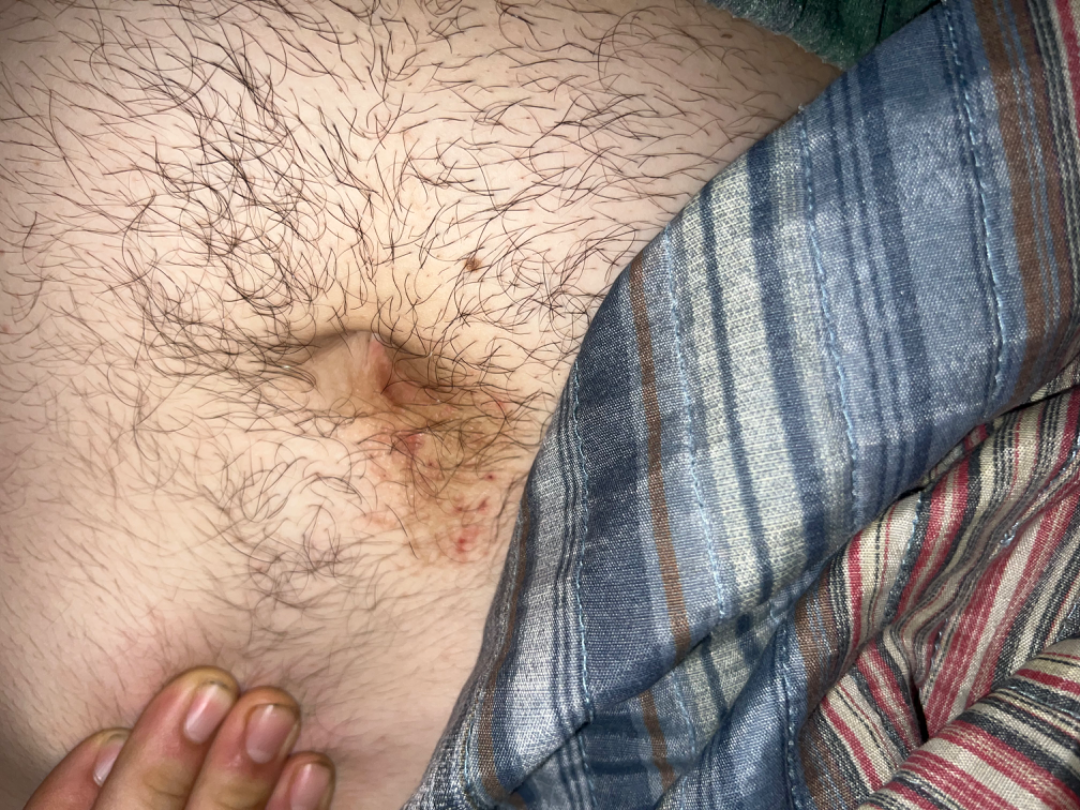<summary>
  <patient>male, age 18–29</patient>
  <shot_type>at an angle</shot_type>
  <differential>
    <Contact dermatitis>0.35</Contact dermatitis>
    <Candidal intertrigo>0.35</Candidal intertrigo>
    <Scabies>0.18</Scabies>
    <Dermatosis caused by lice>0.12</Dermatosis caused by lice>
  </differential>
</summary>